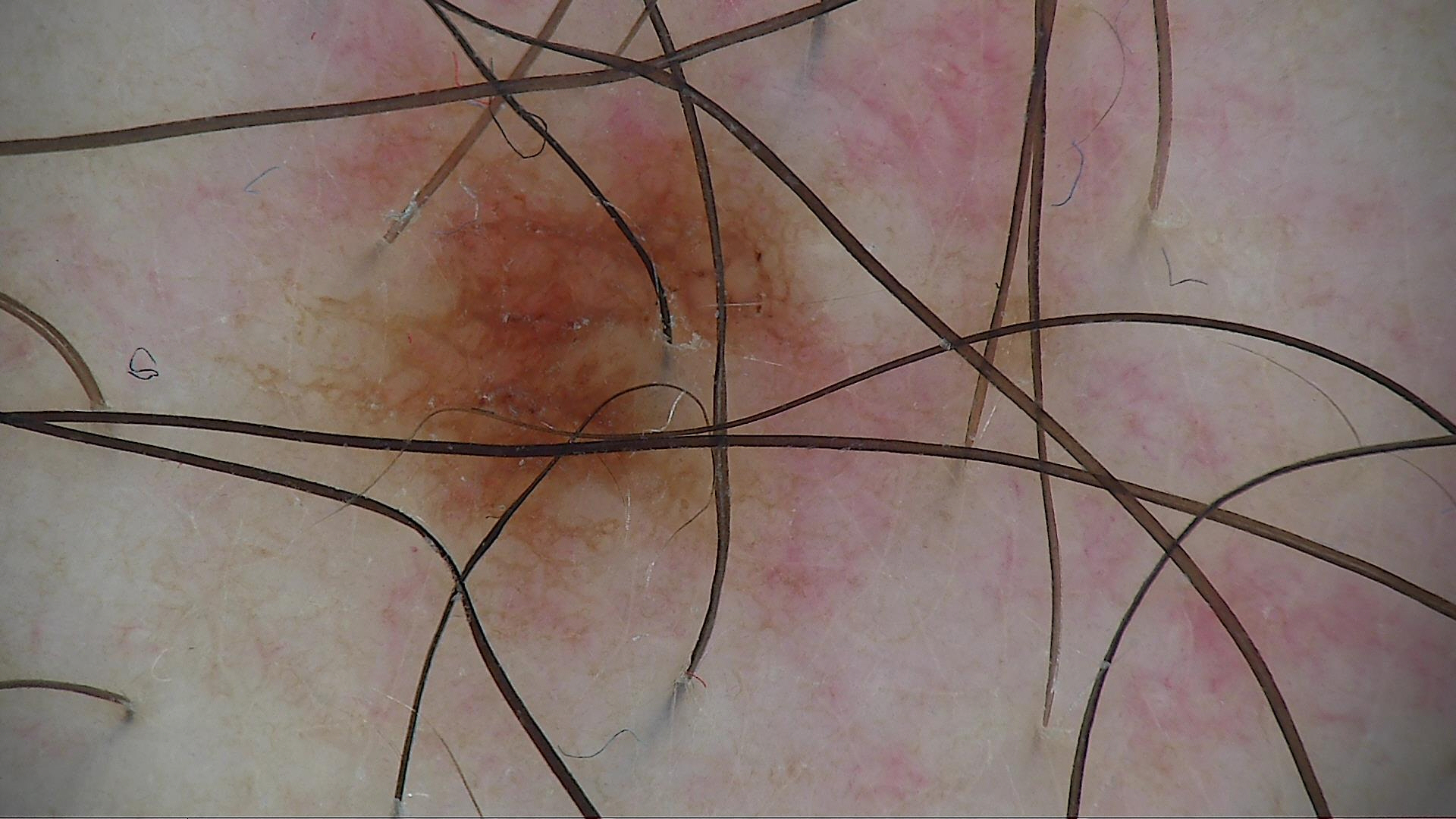Impression: Classified as a compound nevus.